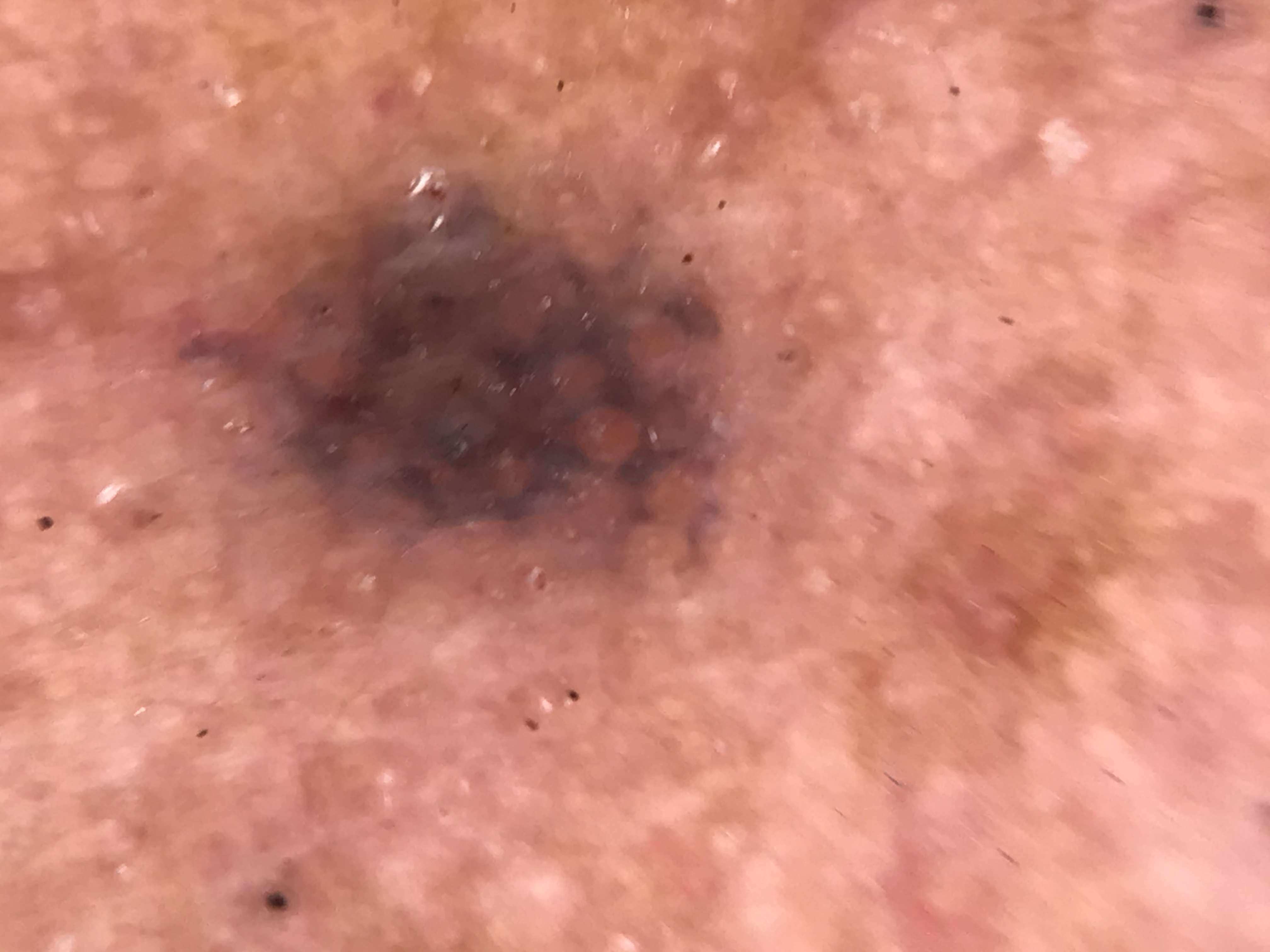modality = dermatoscopy; category = compound, banal; class = Miescher nevus (expert consensus).